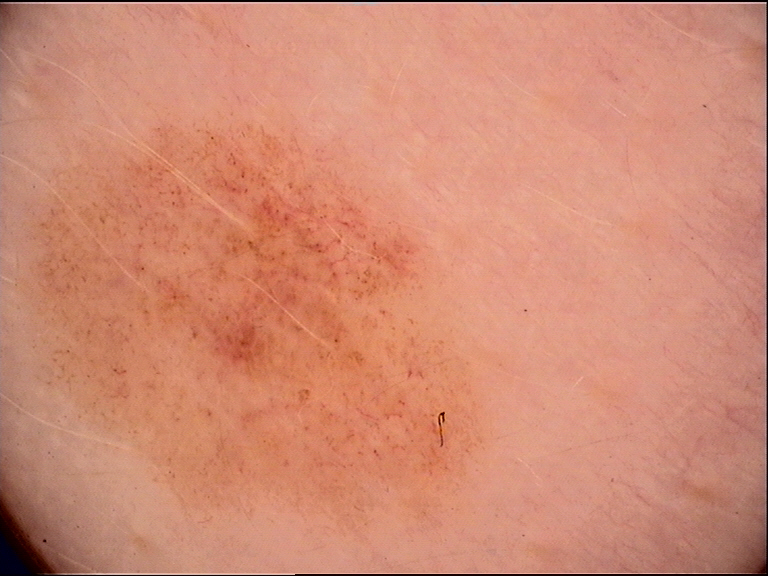imaging = dermoscopy, label = dysplastic junctional nevus (expert consensus).